A dermoscopic close-up of a skin lesion: 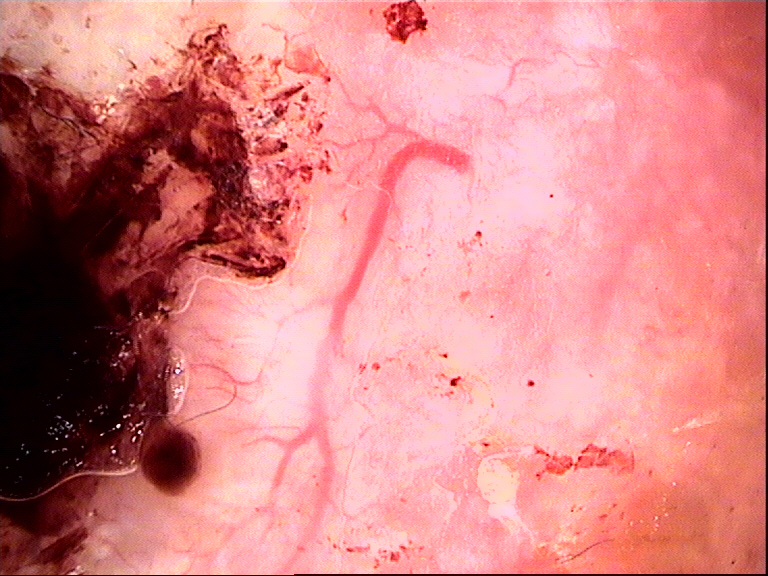This is a keratinocytic lesion. The biopsy diagnosis was a basal cell carcinoma.